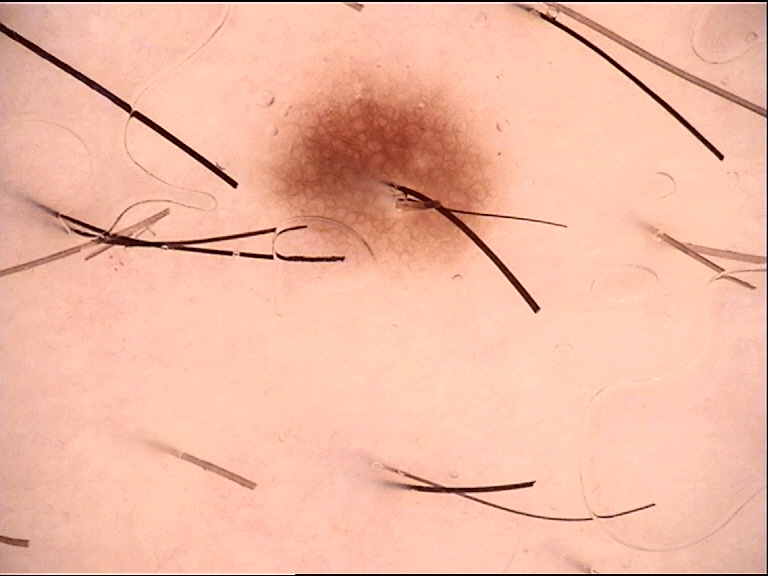image=dermatoscopy; label=dysplastic junctional nevus (expert consensus).